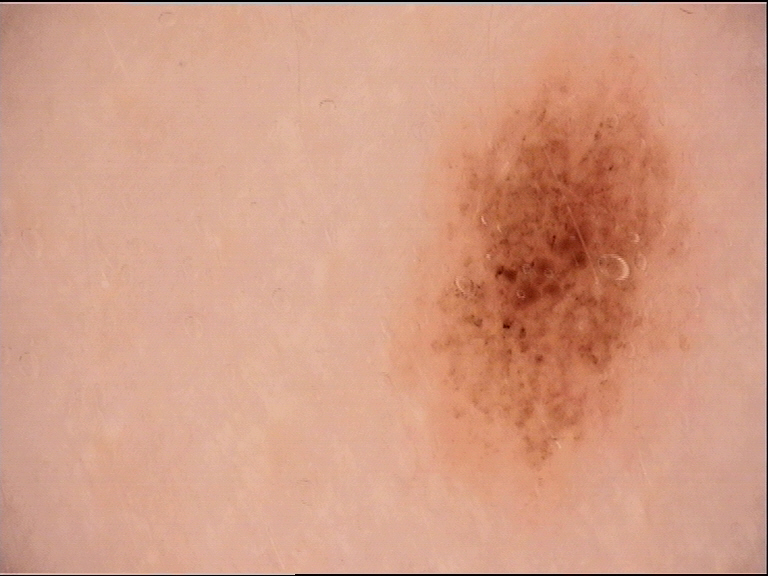Case:
* imaging · dermatoscopy
* label · dysplastic junctional nevus (expert consensus)